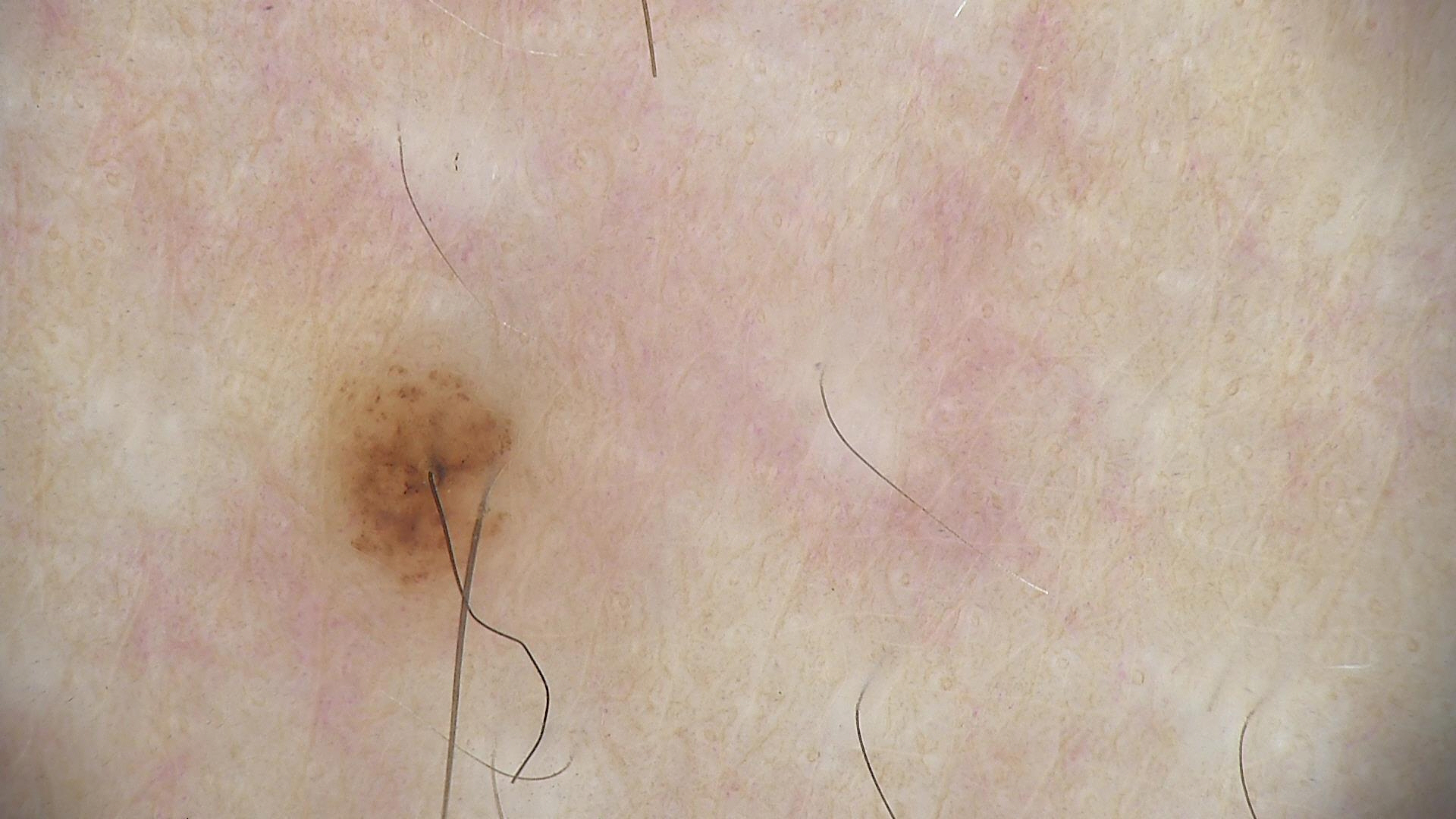class: dysplastic junctional nevus (expert consensus)